A dermoscopic close-up of a skin lesion · a male patient roughly 60 years of age: 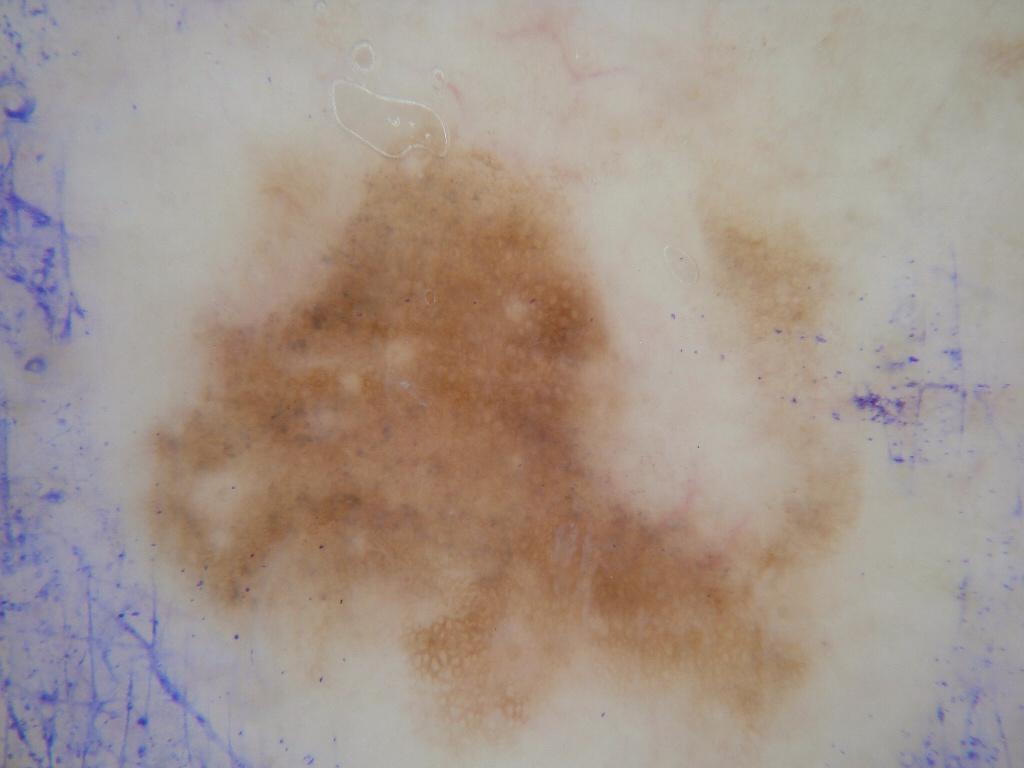{
  "lesion_extent": "large",
  "dermoscopic_features": {
    "present": [
      "pigment network"
    ],
    "absent": [
      "streaks",
      "milia-like cysts",
      "globules",
      "negative network"
    ]
  },
  "lesion_location": {
    "bbox_xyxy": [
      111,
      91,
      868,
      766
    ]
  },
  "diagnosis": {
    "name": "melanocytic nevus",
    "malignancy": "benign",
    "lineage": "melanocytic",
    "provenance": "clinical"
  }
}